A male subject, roughly 55 years of age · dermoscopy of a skin lesion:
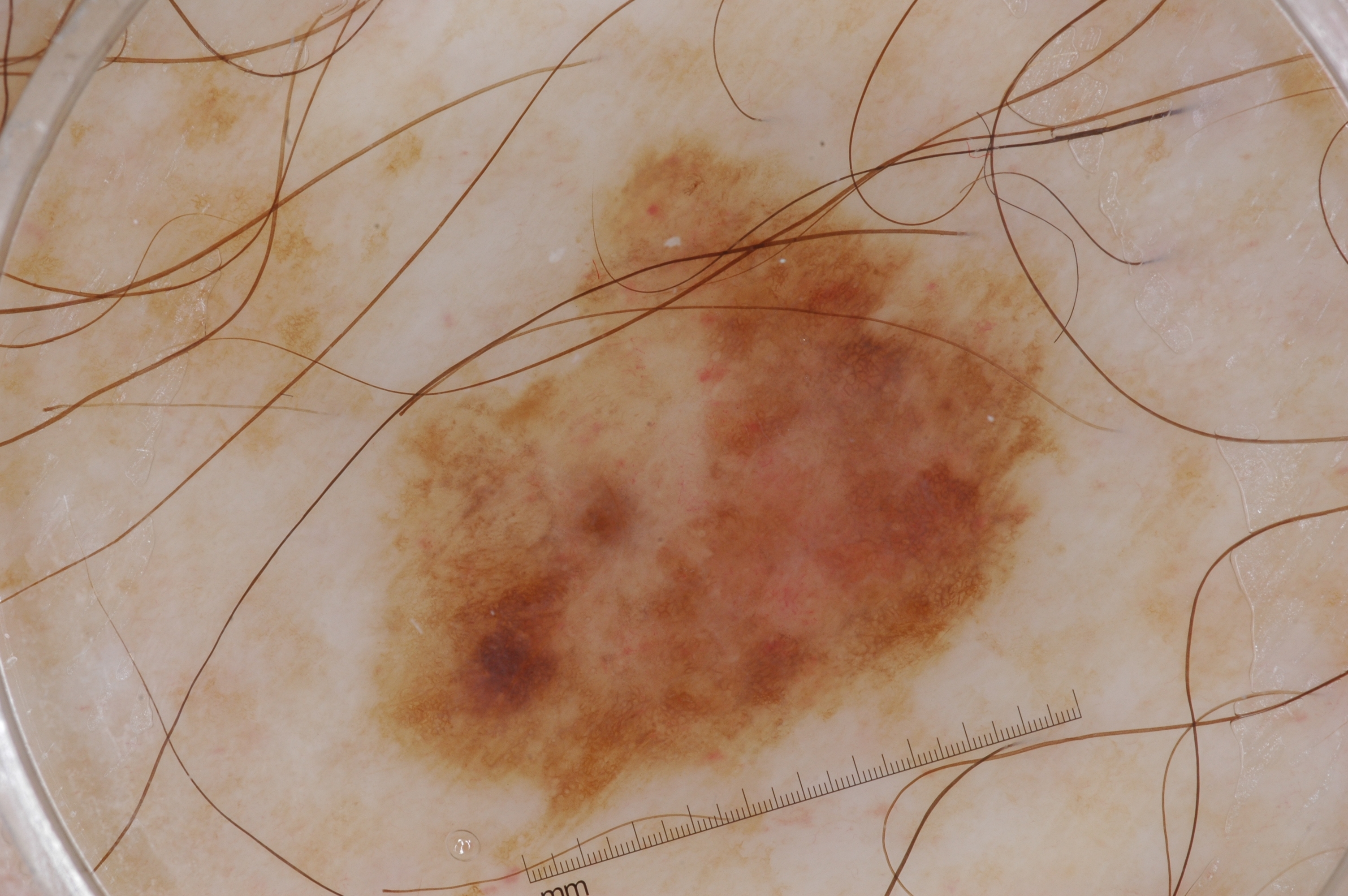{"dermoscopic_features": {"present": ["pigment network", "milia-like cysts"], "absent": ["negative network", "streaks"]}, "lesion_location": {"bbox_xyxy": [379, 140, 1053, 812]}, "diagnosis": {"name": "melanoma", "malignancy": "malignant", "lineage": "melanocytic", "provenance": "histopathology"}}